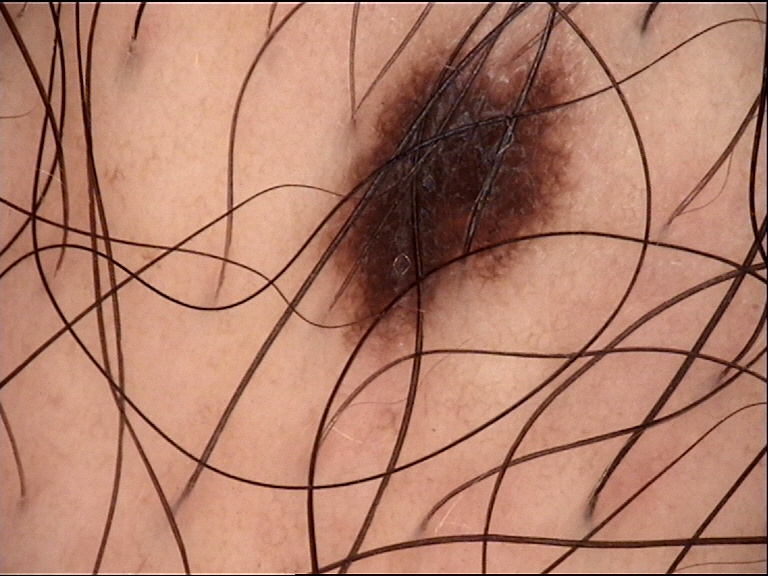Case: A dermoscopic close-up of a skin lesion. Conclusion: The diagnostic label was a banal lesion — a junctional nevus.